Contact-polarized dermoscopy of a skin lesion · a female patient approximately 70 years of age · recorded as skin type II: 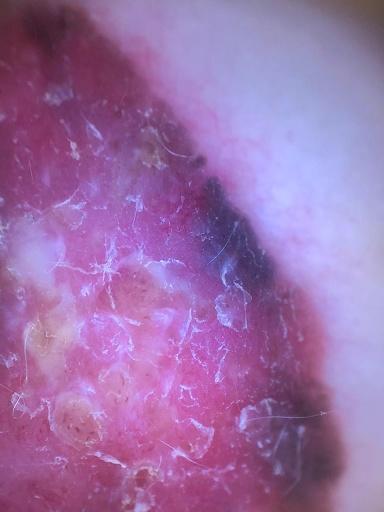Image and clinical context:
The lesion involves a lower extremity.
Conclusion:
Biopsy-confirmed as a malignancy — a melanoma.